Reported duration is one to four weeks · the patient did not report lesion symptoms · an image taken at an angle · the lesion involves the head or neck · skin tone: Fitzpatrick IV; human graders estimated MST 5 (US pool) or 3 (India pool) · the patient is 40–49, male · the lesion is described as raised or bumpy — 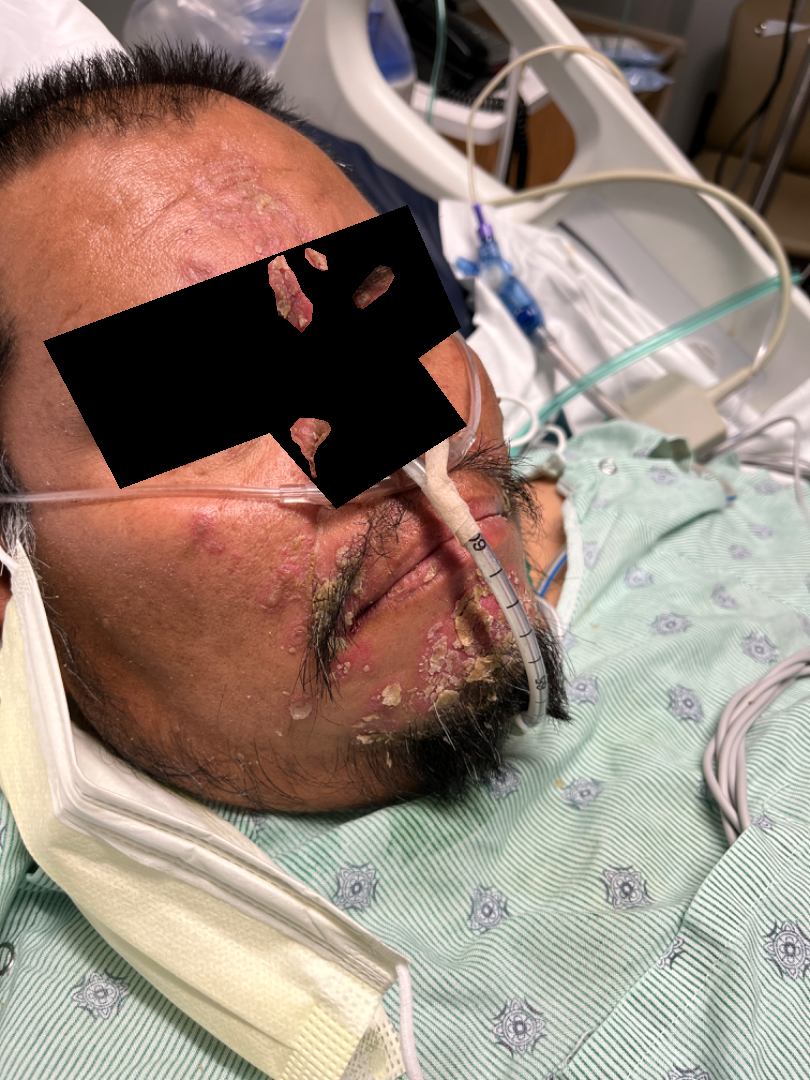On remote review of the image, the favored diagnosis is Seborrheic Dermatitis; the differential also includes Pemphigus.